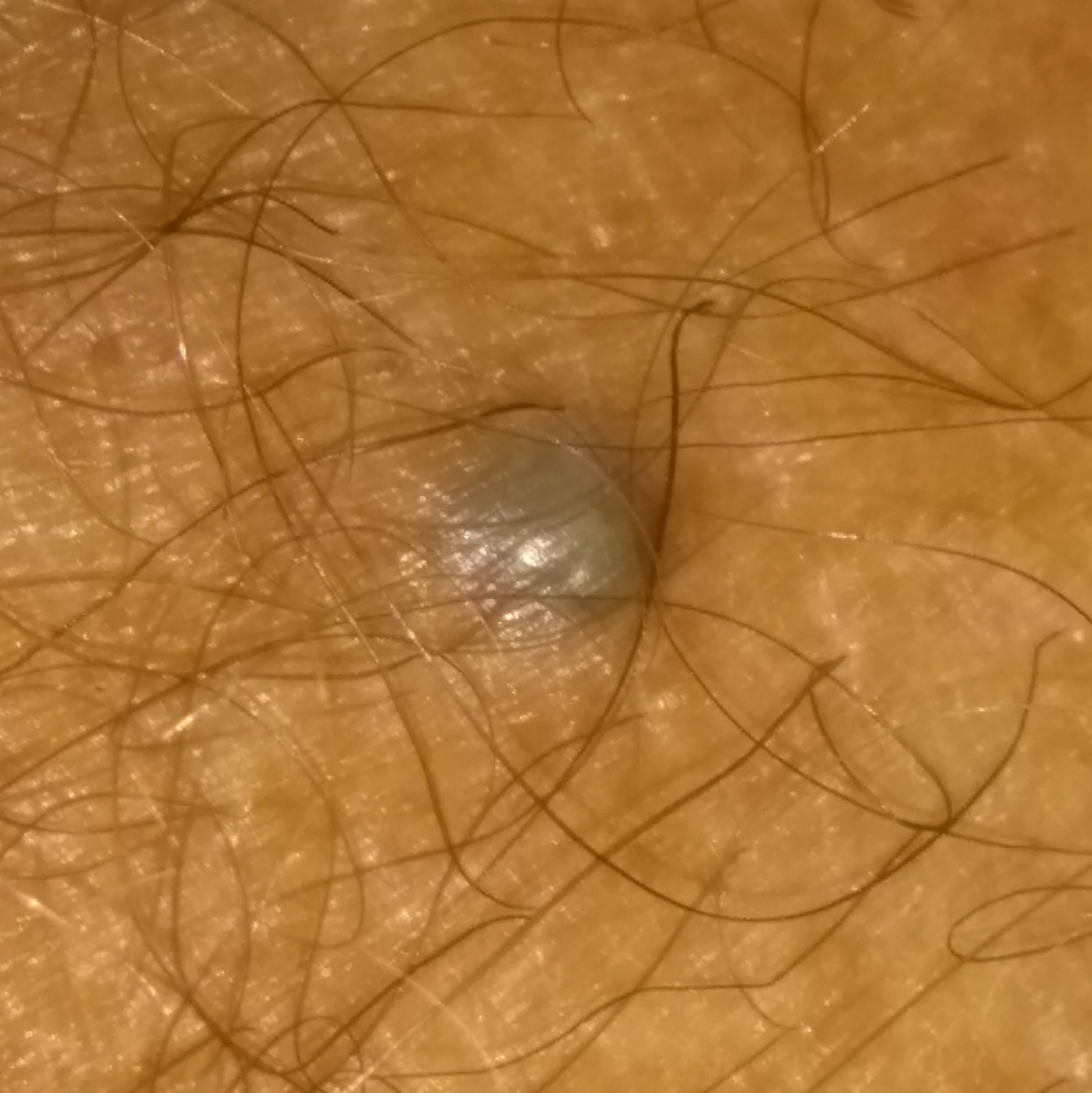Expert review favored a nevus.